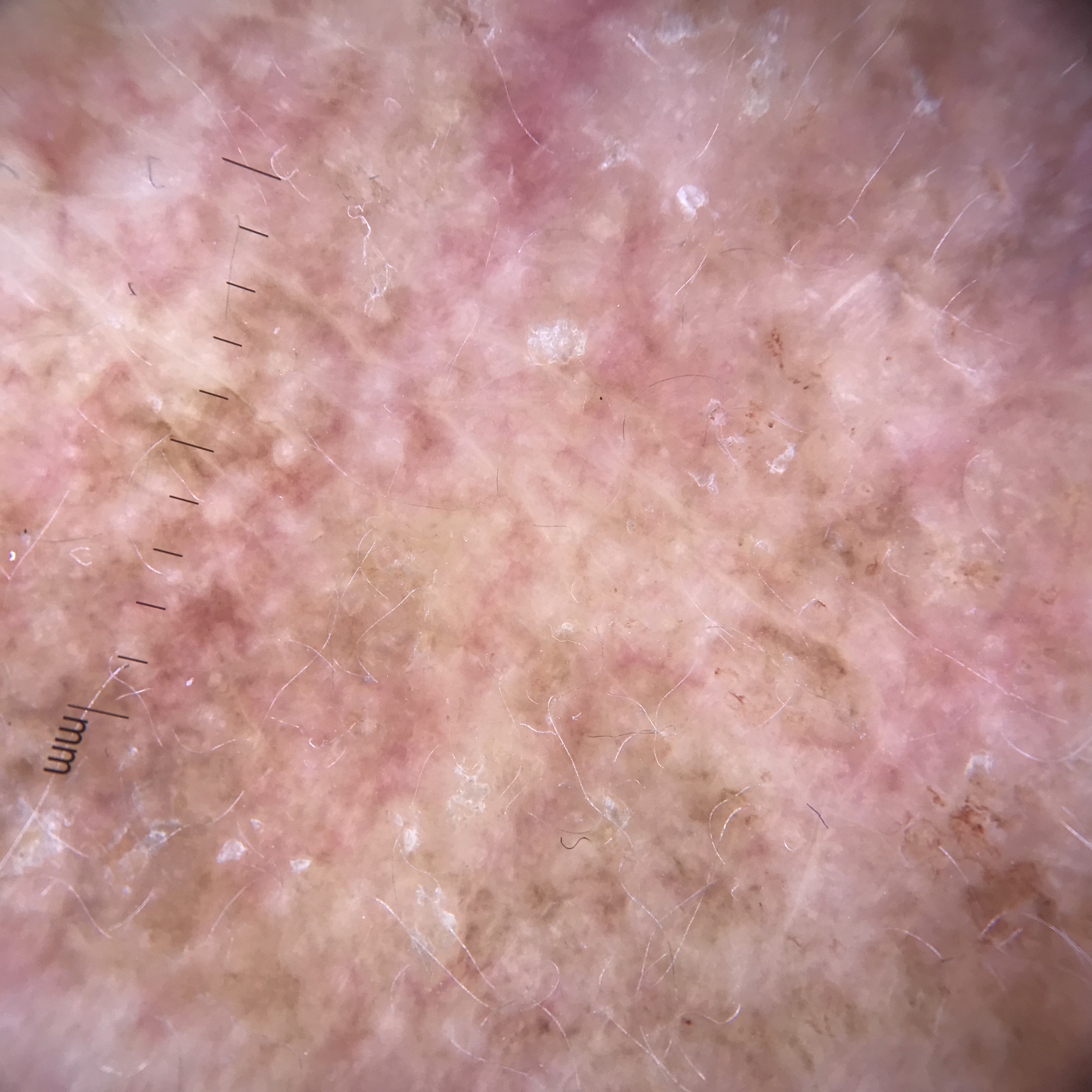A dermoscopic image of a skin lesion.
The architecture is that of a keratinocytic lesion.
Classified as a lesion of indeterminate malignant potential — an actinic keratosis.